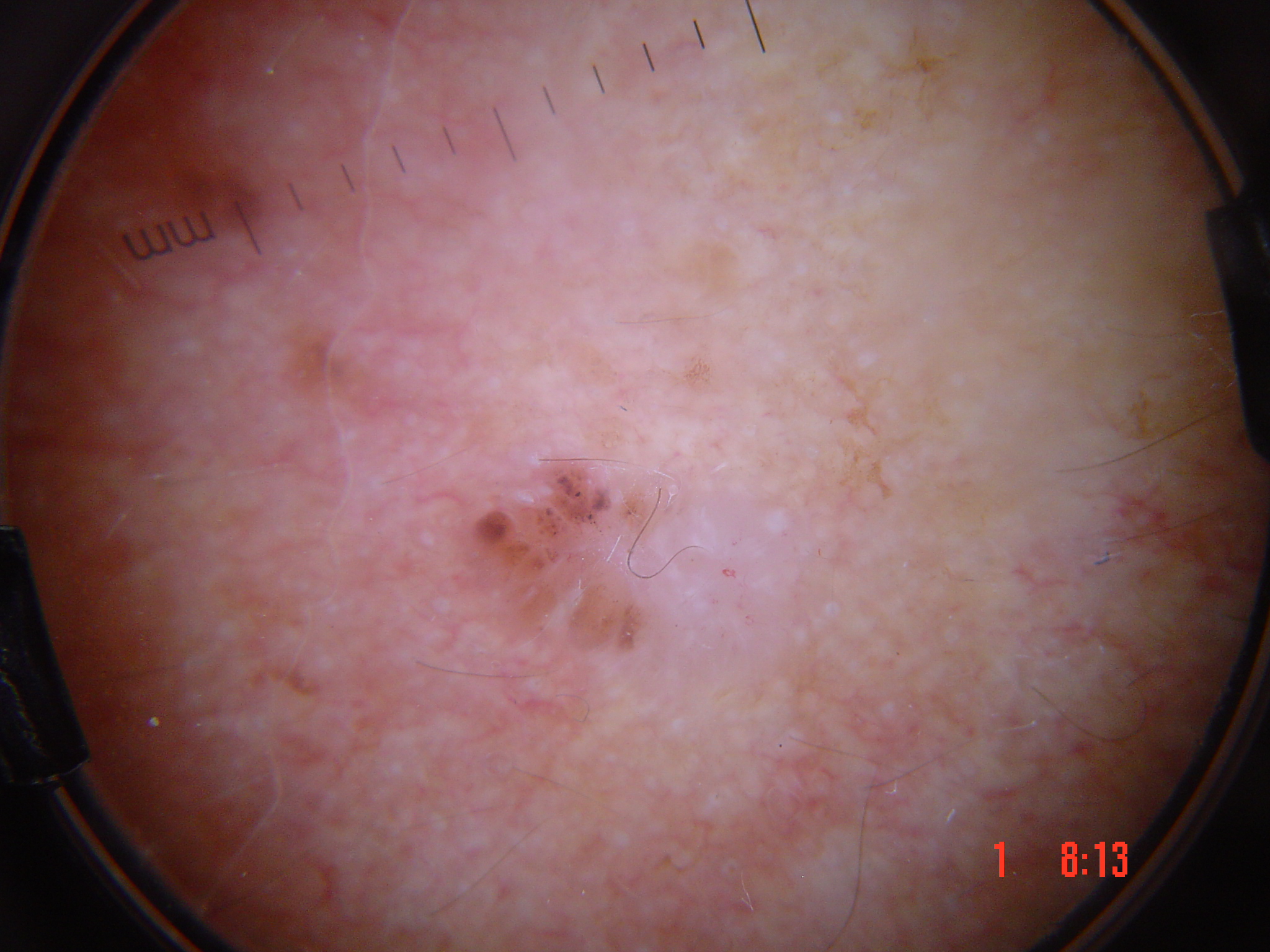| feature | finding |
|---|---|
| image | dermatoscopy |
| subtype | keratinocytic |
| diagnostic label | basal cell carcinoma (biopsy-proven) |